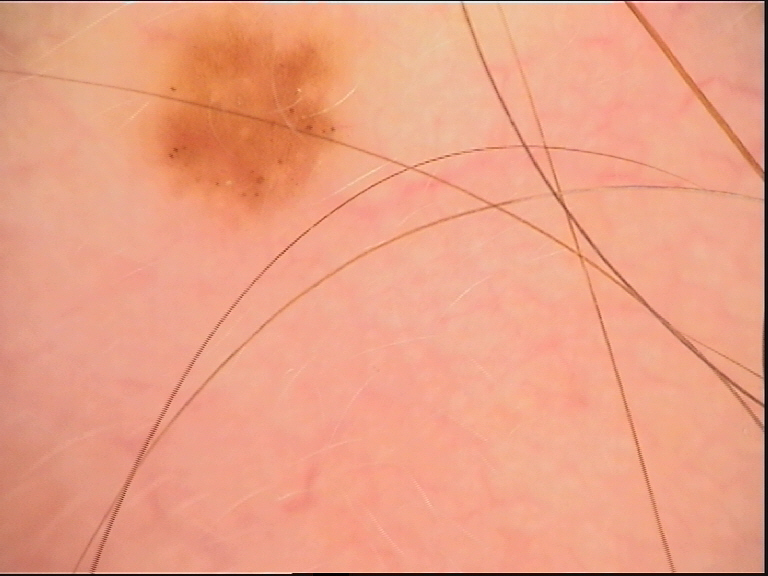Summary: A dermoscopic image of a skin lesion. Impression: The diagnosis was a dysplastic junctional nevus.